A subject in their 60s:
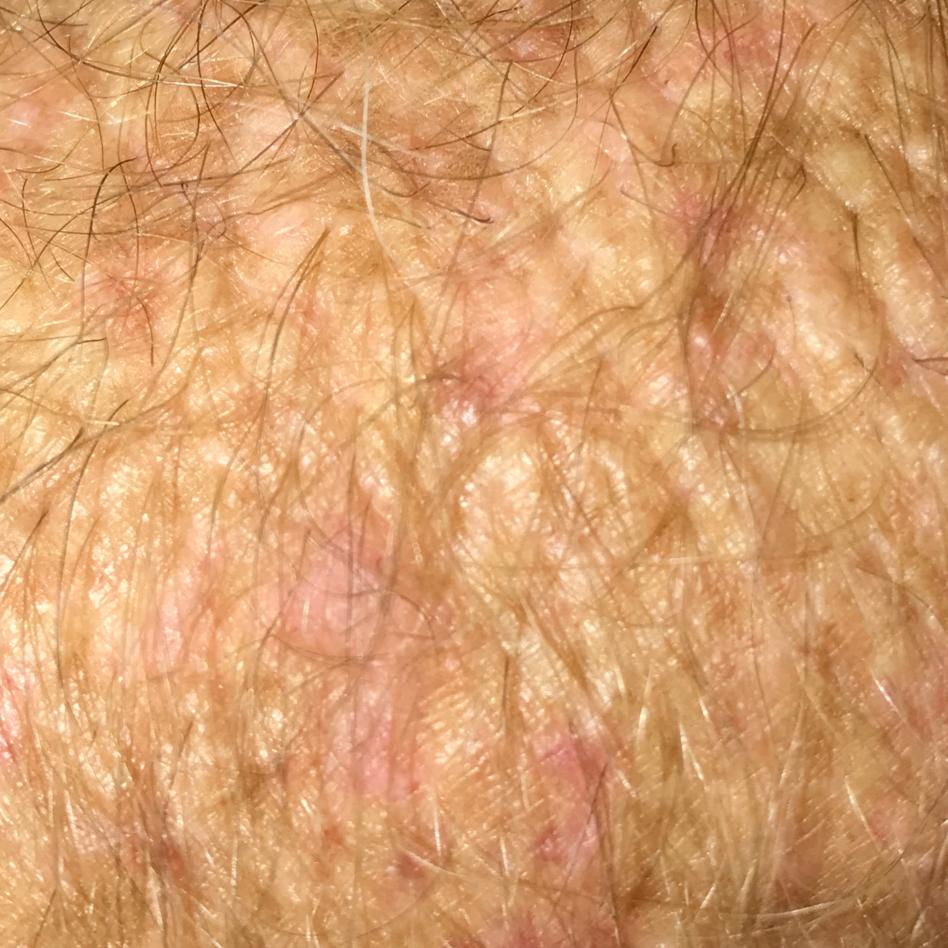The lesion was found on a forearm. The diagnostic impression was a lesion with uncertain malignant potential — an actinic keratosis.